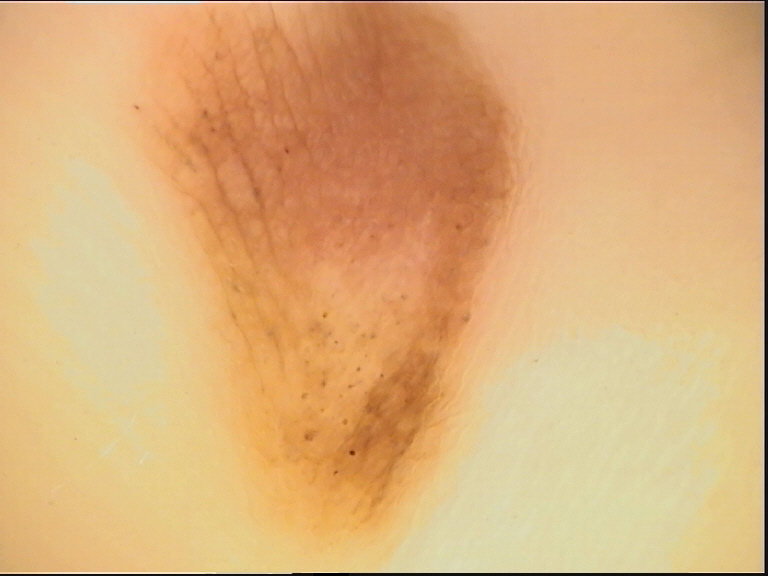{"image": "dermoscopy", "diagnosis": {"name": "acral dysplastic compound nevus", "code": "acd", "malignancy": "benign", "super_class": "melanocytic", "confirmation": "expert consensus"}}